A clinical photo of a skin lesion taken with a smartphone — 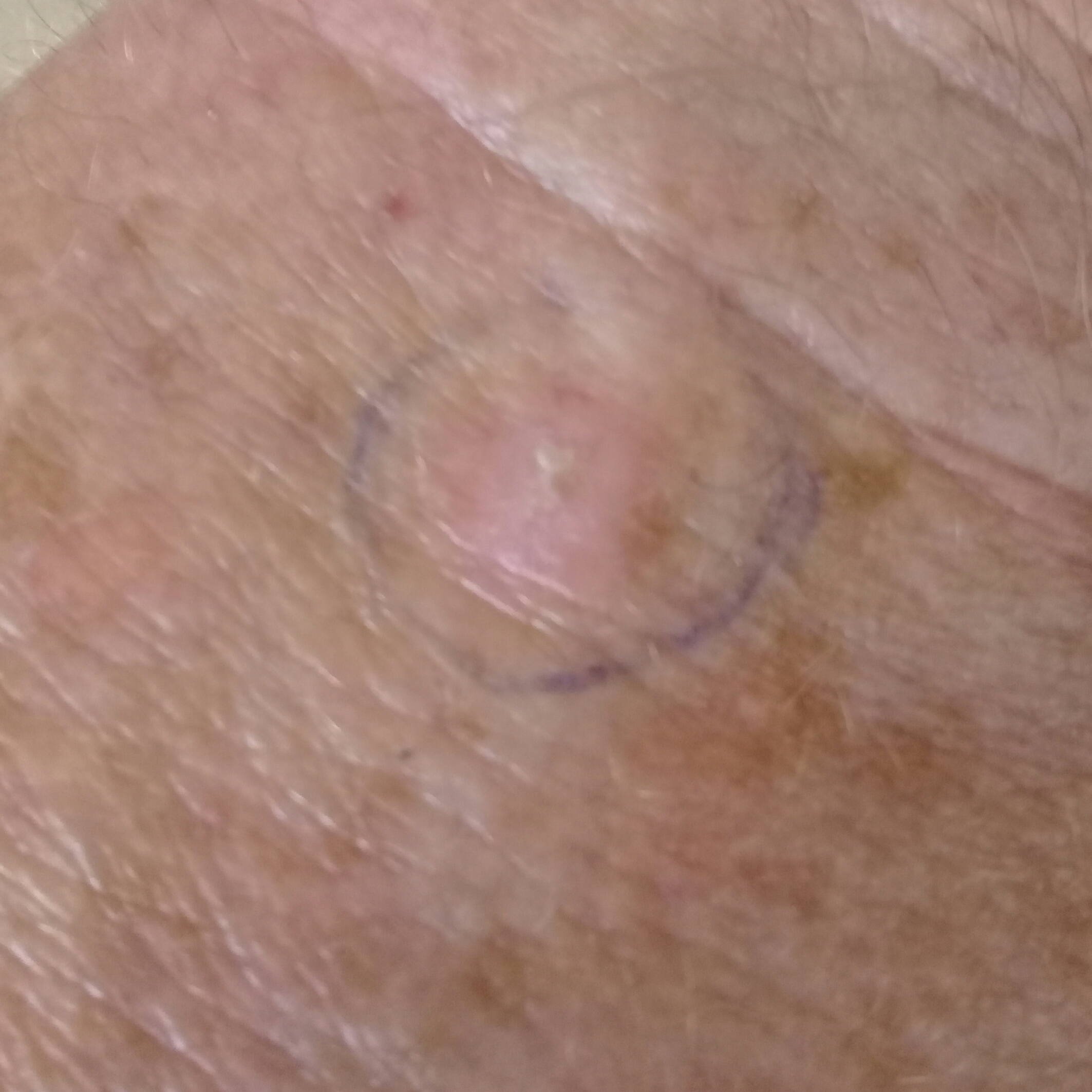Per patient report, the lesion has bled and is elevated, but does not itch and does not hurt.
Clinically diagnosed as an actinic keratosis.